Fitzpatrick III · the lesion is described as raised or bumpy and fluid-filled · the patient reports associated fatigue, chills and joint pain · the patient reports burning, bleeding, itching and pain · the lesion involves the back of the torso, back of the hand, arm and leg · an image taken at a distance · reported duration is one to four weeks · the patient considered this a rash: 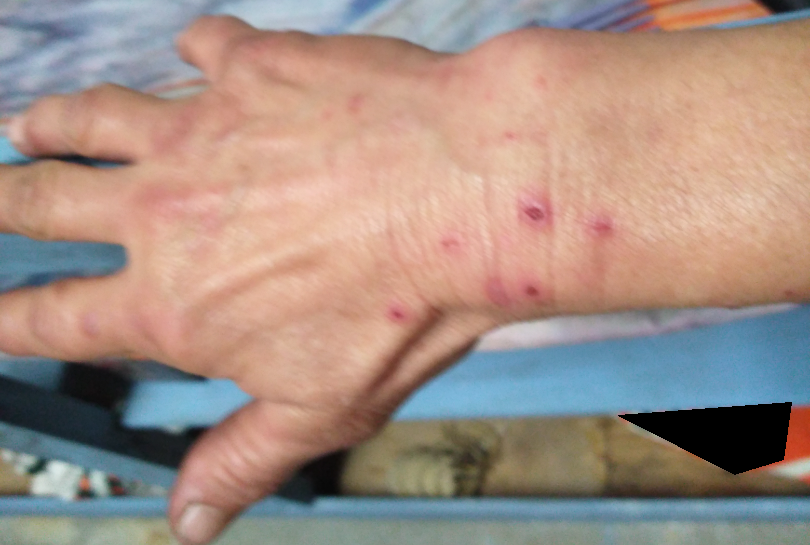  differential:
    leading:
      - Prurigo nodularis